A skin lesion imaged with a dermatoscope · the subject is a male approximately 15 years of age.
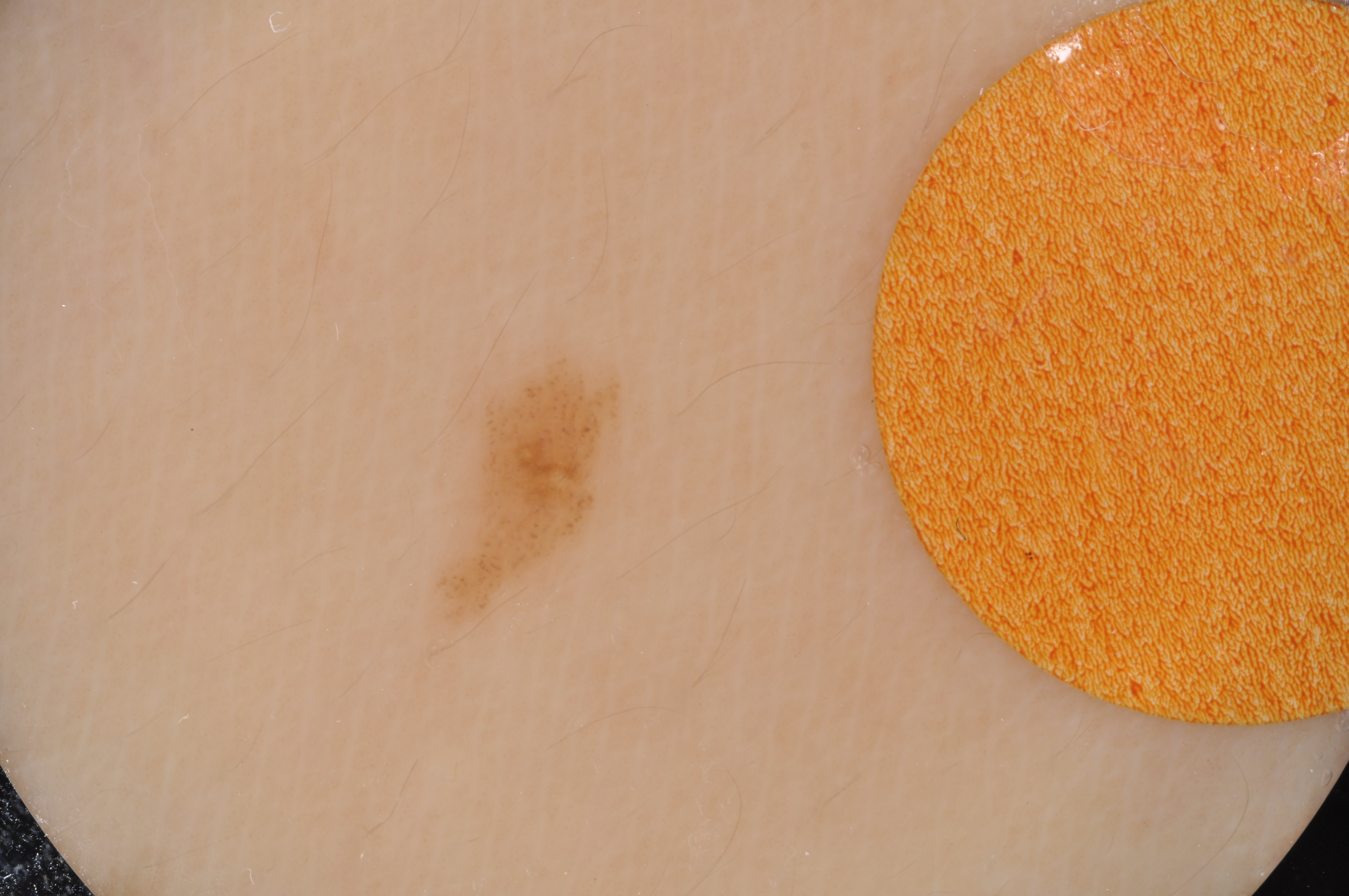lesion location = 427, 350, 630, 634
absent dermoscopic features = negative network, streaks, pigment network, and milia-like cysts
lesion extent = small
diagnostic label = a melanocytic nevus, a benign skin lesion